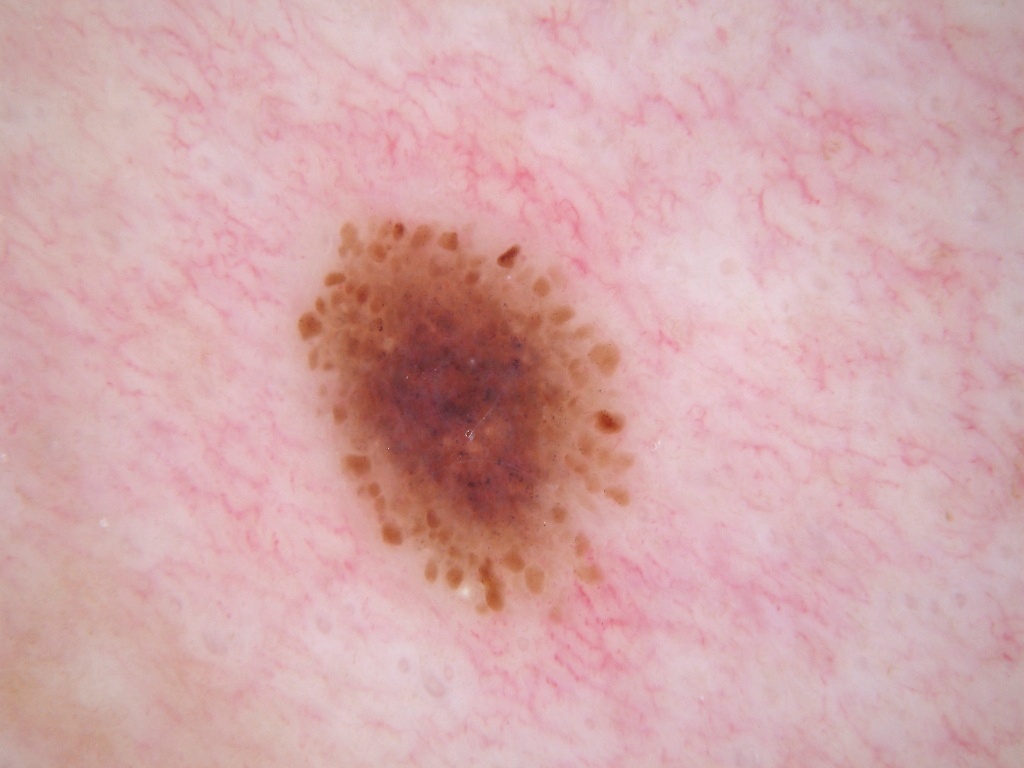Dermoscopy of a skin lesion. The patient is a female aged approximately 30. With coordinates (x1, y1, x2, y2), the lesion occupies the region [296,212,630,622]. Dermoscopic examination shows globules and milia-like cysts. The lesion takes up about 12% of the image. Expert review diagnosed this as a melanocytic nevus, a benign lesion.